A dermatoscopic image of a skin lesion — 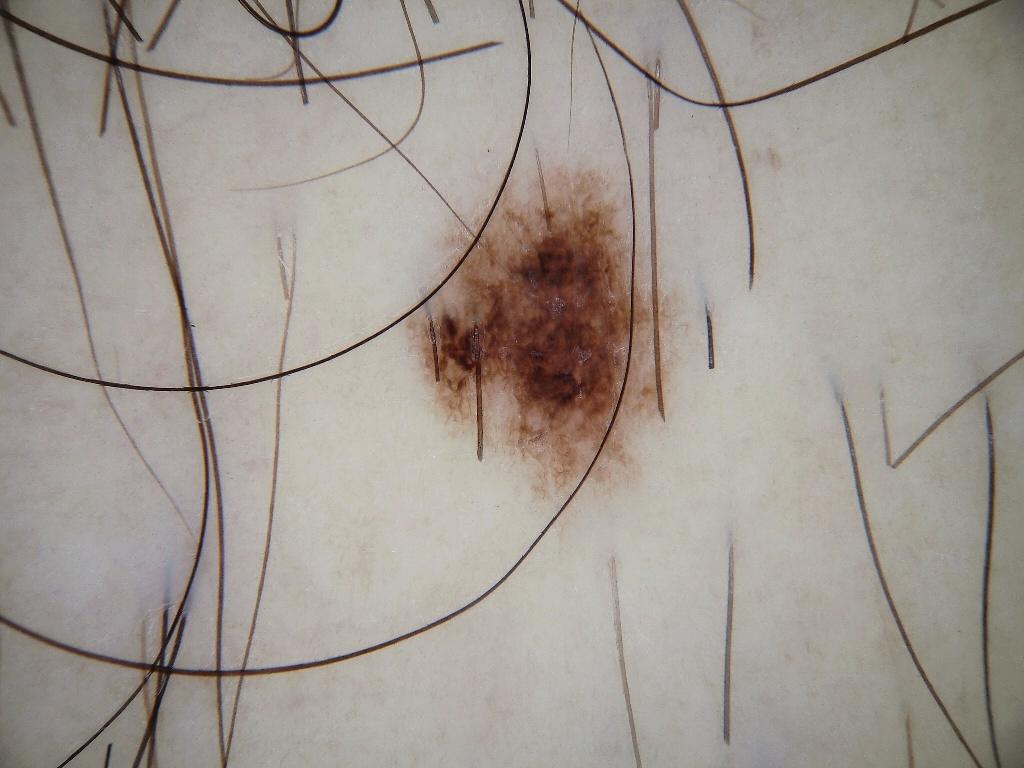Findings:
* location · bbox=[392, 150, 695, 539]
* diagnostic label · a benign skin lesion